The patient describes having a moderate number of moles. The patient reports a personal history of cancer, no sunbed use, and no family history of skin cancer. A dermoscopy image of a skin lesion. Imaged for a research study, with no referral diagnosis recorded. The patient says their skin tans without first burning — 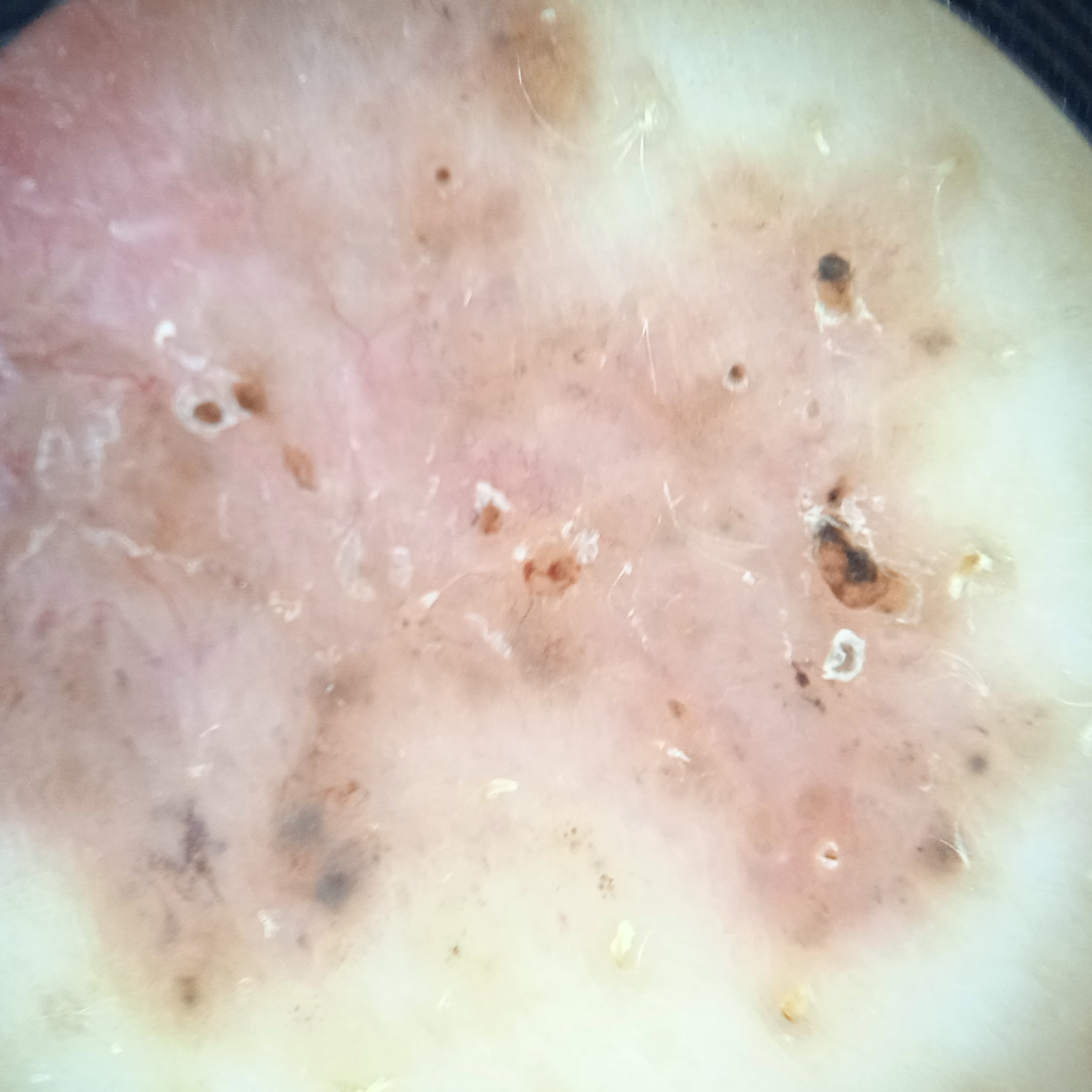The lesion is located on the back. The lesion was assessed as a basal cell carcinoma.